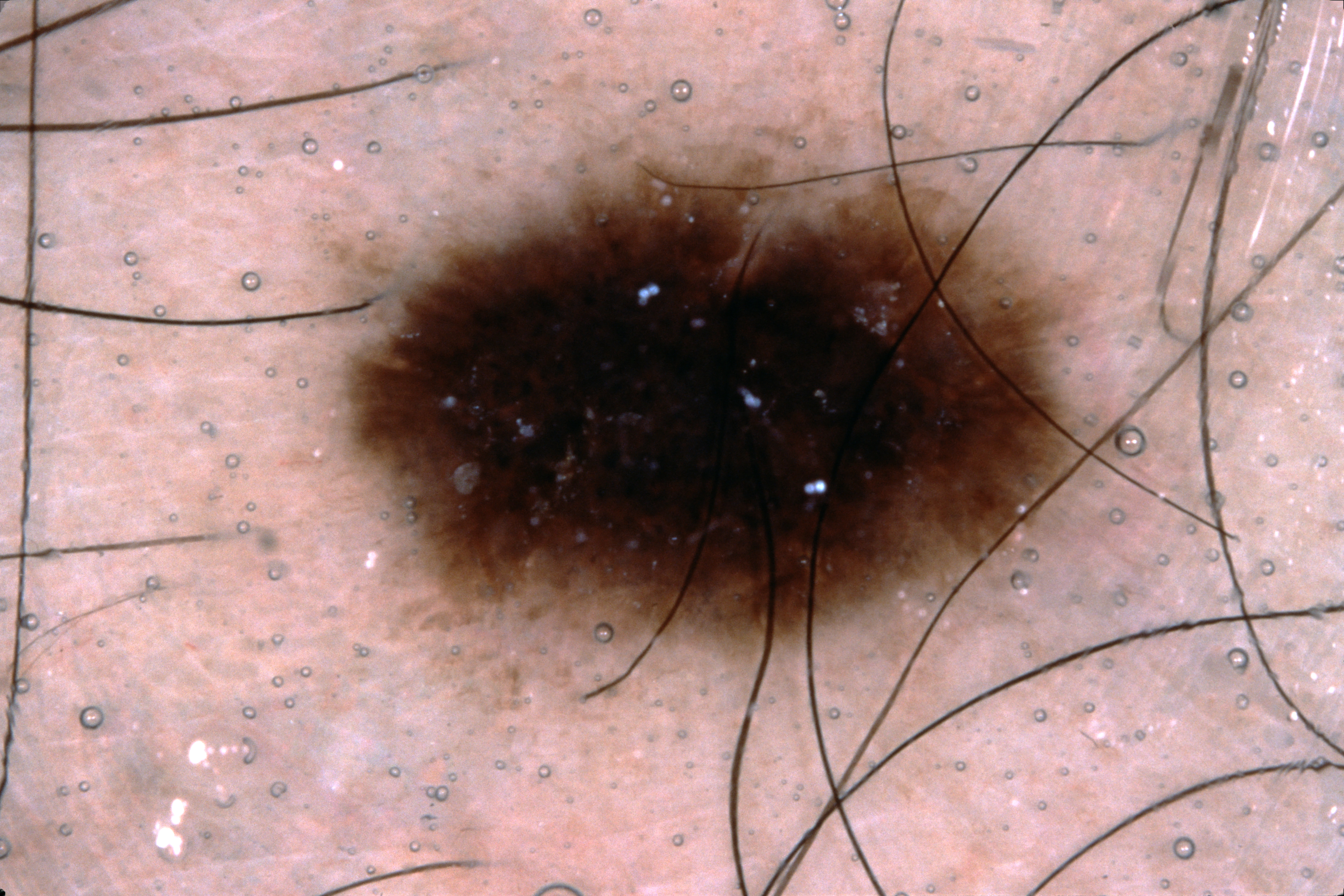A dermoscopic close-up of a skin lesion. A male patient, aged approximately 40. Dermoscopically, the lesion shows no streaks, milia-like cysts, pigment network, or negative network. In (x1, y1, x2, y2) order, lesion location: <bbox>330, 102, 1145, 707</bbox>. A prominent lesion filling much of the field. The lesion was assessed as a melanocytic nevus, a benign skin lesion.